The patient notes pain, the patient described the issue as a rash, the patient notes the lesion is rough or flaky, skin tone: Fitzpatrick skin type I, the affected area is the leg, present for about one day, close-up view: 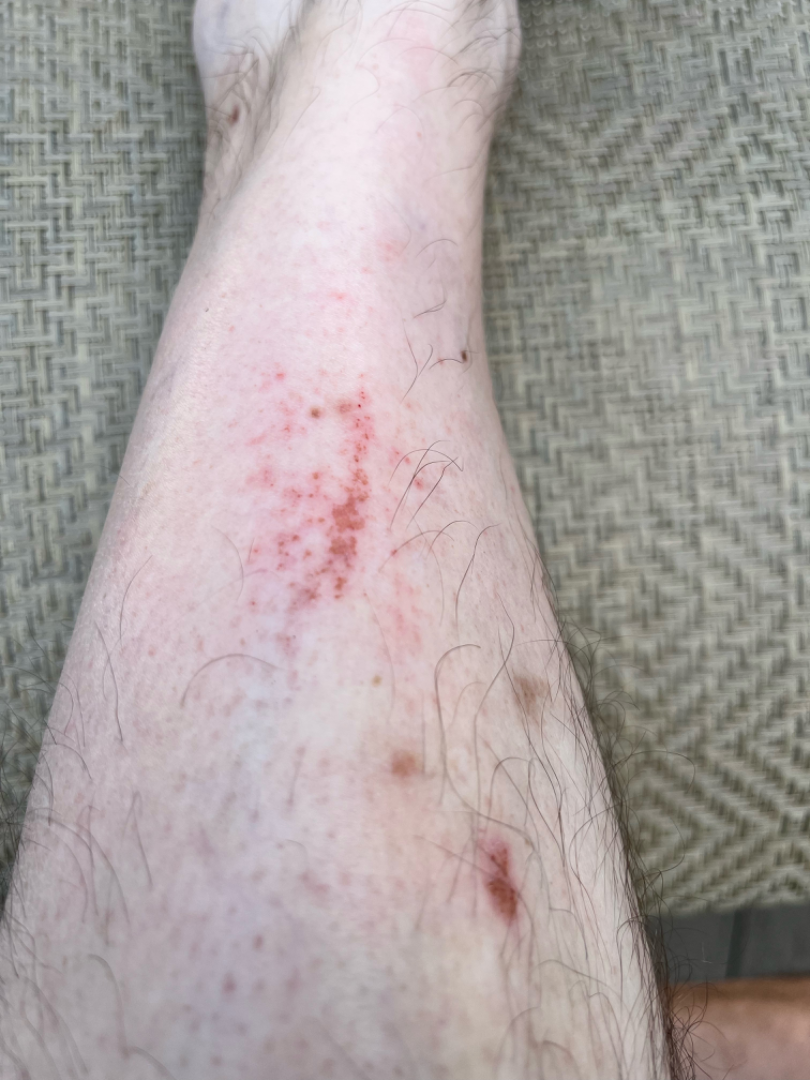On remote dermatologist review: the differential is split between Abrasion, scrape, or scab and Eczema.